A dermoscopic image of a skin lesion.
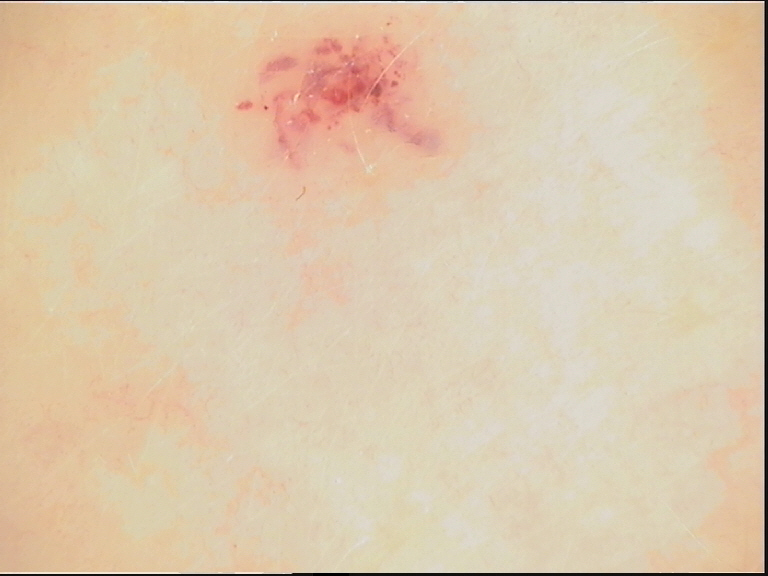lesion type: vascular; assessment: hemangioma (expert consensus).